A subject aged 67: 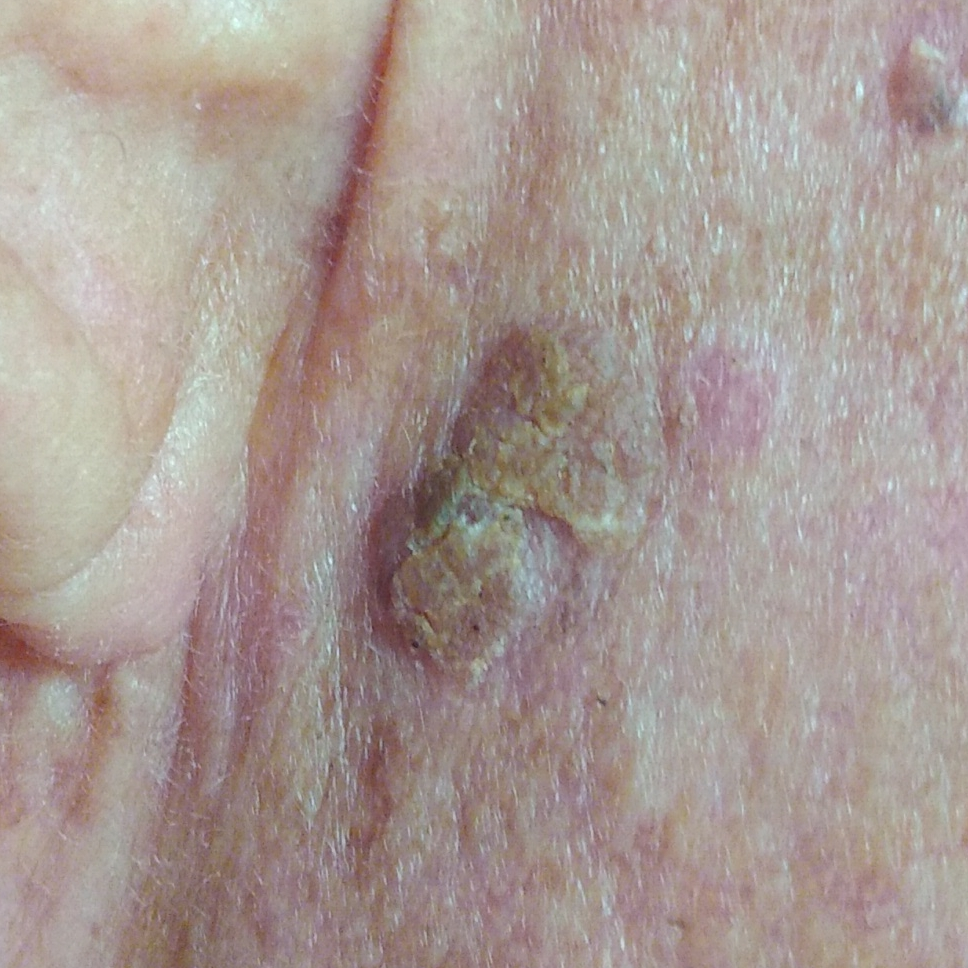Q: Where on the body is the lesion?
A: the face
Q: What does the patient describe?
A: elevation, itching, growth / no pain, no change in appearance
Q: What is the diagnosis?
A: seborrheic keratosis (clinical consensus)